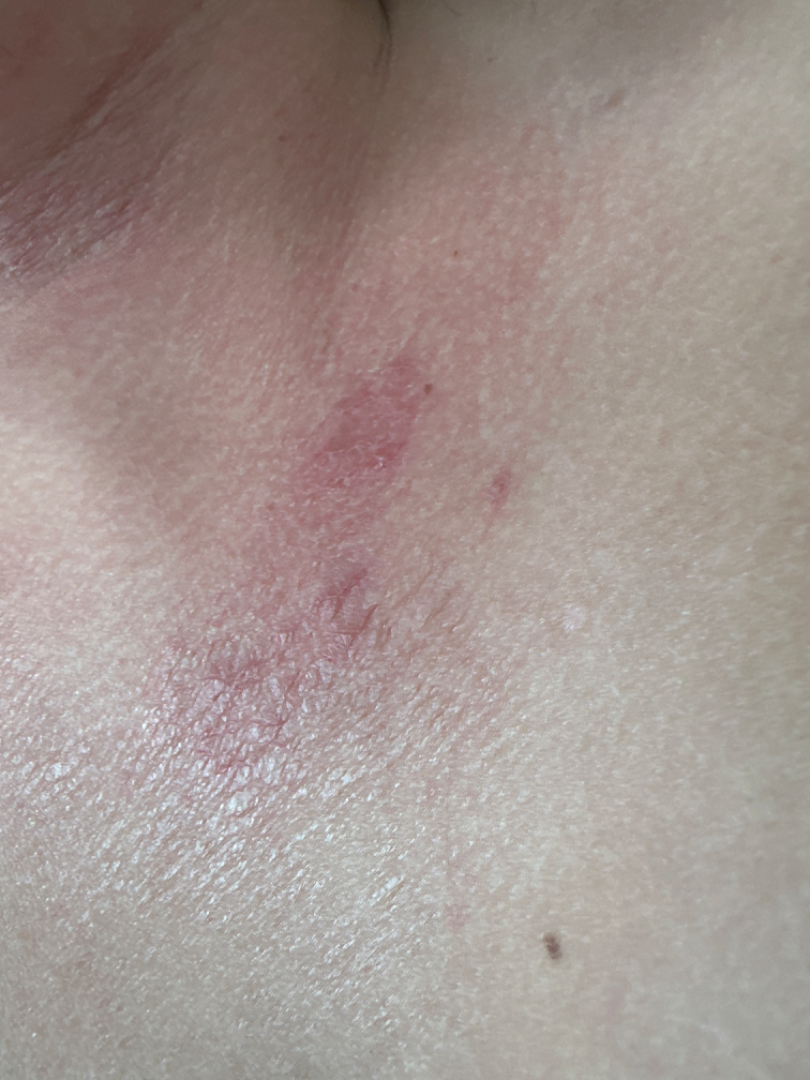The case was difficult to assess from the available photograph. The lesion involves the front of the torso. An image taken at an angle.